The affected area is the arm · the contributor is a female aged 60–69 · the condition has been present for more than five years · close-up view · no relevant lesion symptoms reported — 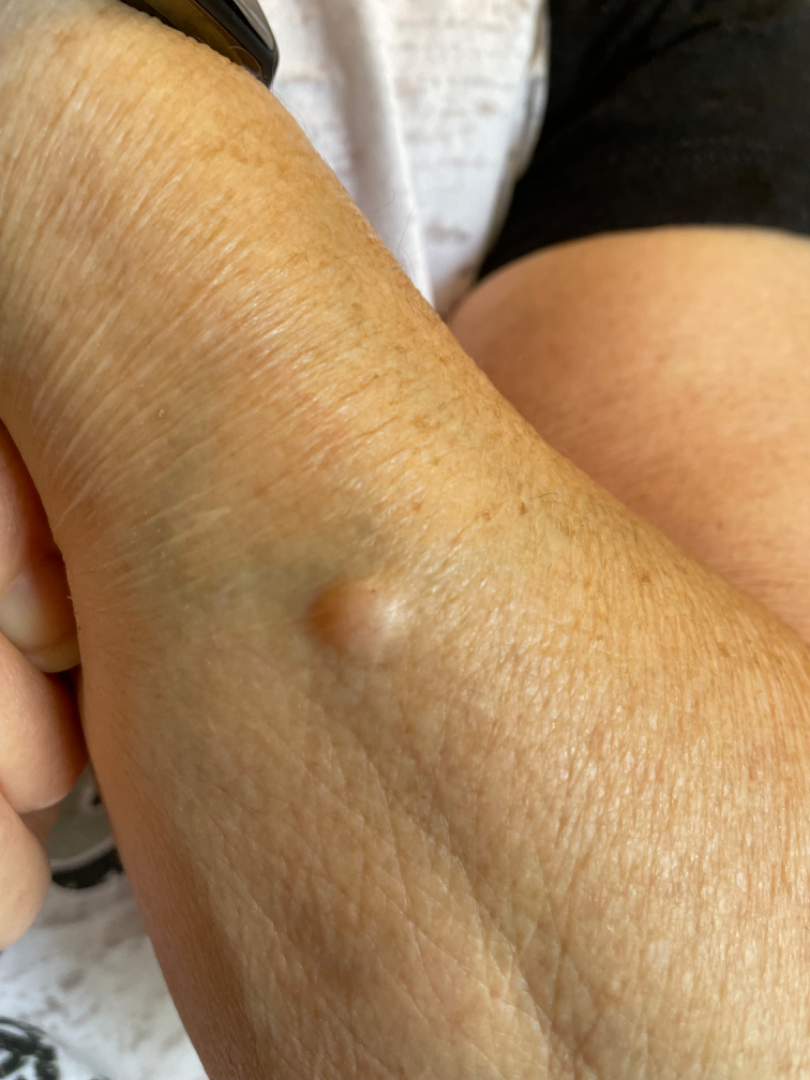assessment: unable to determine